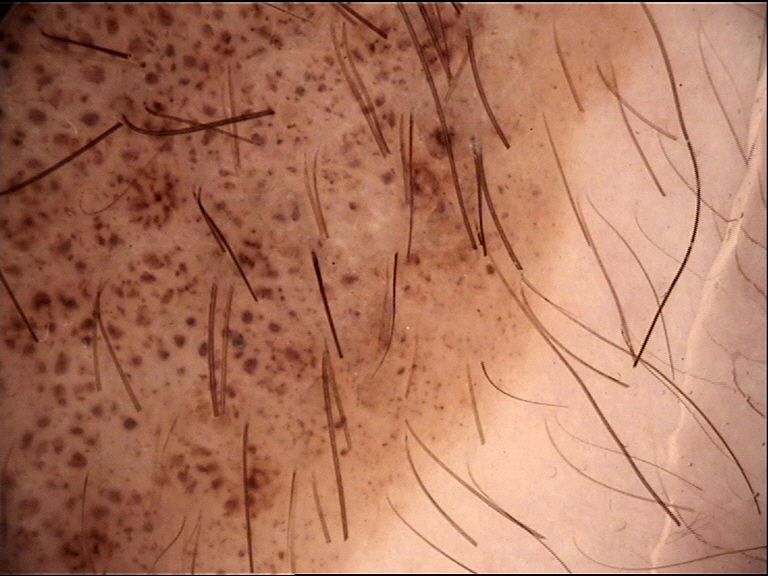The diagnostic label was a congenital compound nevus.